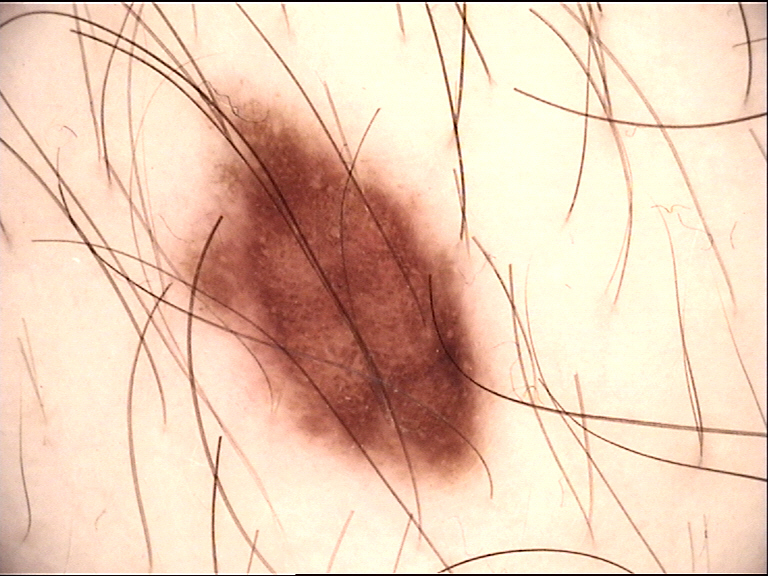Impression:
Diagnosed as a benign lesion — a dysplastic compound nevus.